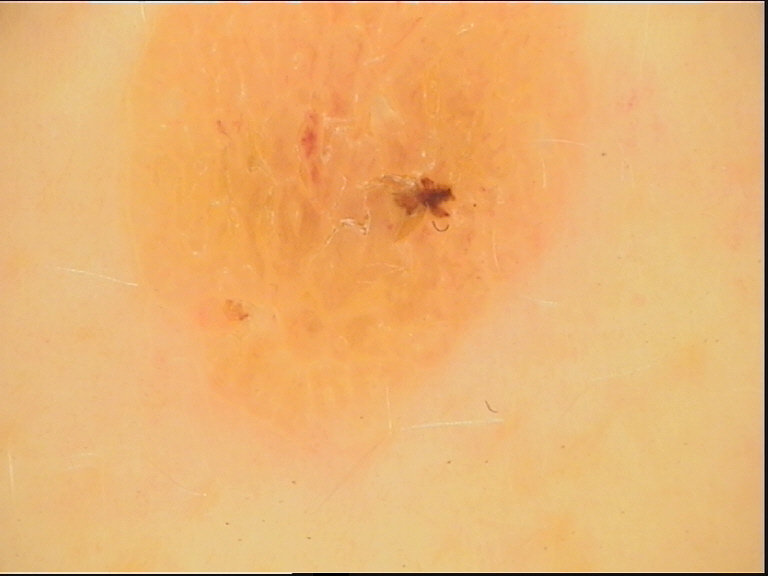diagnostic label=seborrheic keratosis (expert consensus).